A subject 68 years old · a clinical photo of a skin lesion taken with a smartphone:
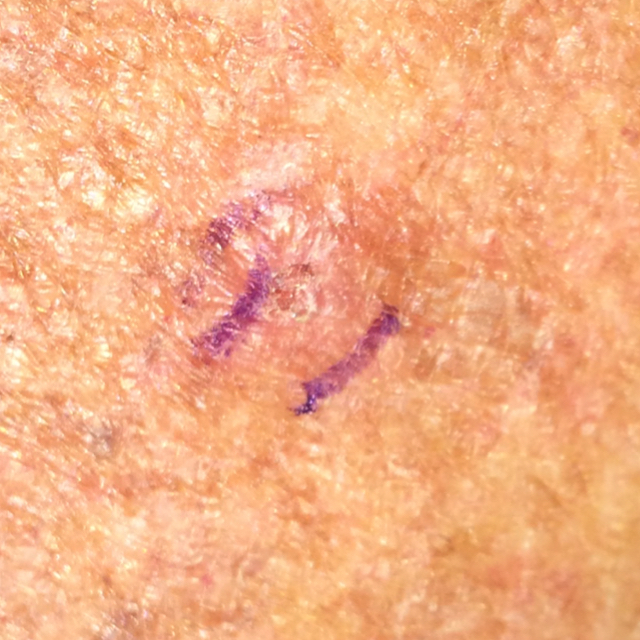location — the chest | reported symptoms — itching, elevation / no change in appearance, no bleeding | impression — actinic keratosis (clinical consensus).